The patient is female; the back of the hand is involved; the photo was captured at an angle:
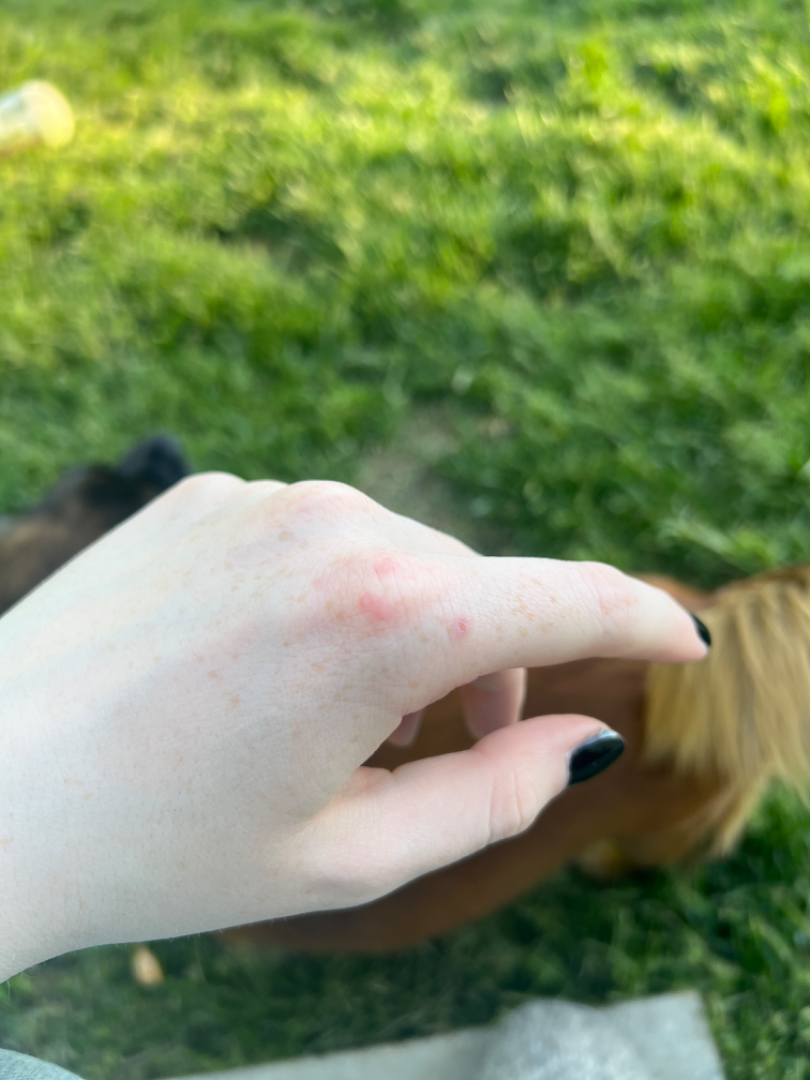The patient described the issue as a rash. The condition has been present for about one day. Reported lesion symptoms include itching. Skin tone: Fitzpatrick I; human graders estimated a Monk skin tone scale of 1. The contributor notes the lesion is raised or bumpy. The favored diagnosis is Allergic Contact Dermatitis.